The chart records prior malignancy (patient or family); a male patient in their mid-40s; the patient was assessed as FST I; a clinical photograph of a skin lesion — 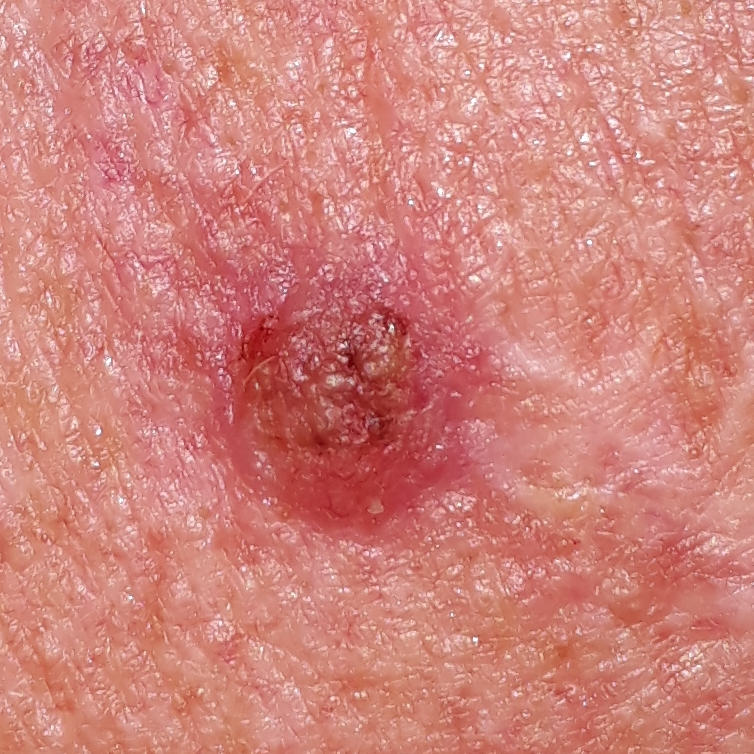Located on the chest.
Measuring about 8 × 6 mm.
The patient reports that the lesion itches, is elevated, has bled, and hurts.
On biopsy, the diagnosis was a basal cell carcinoma.